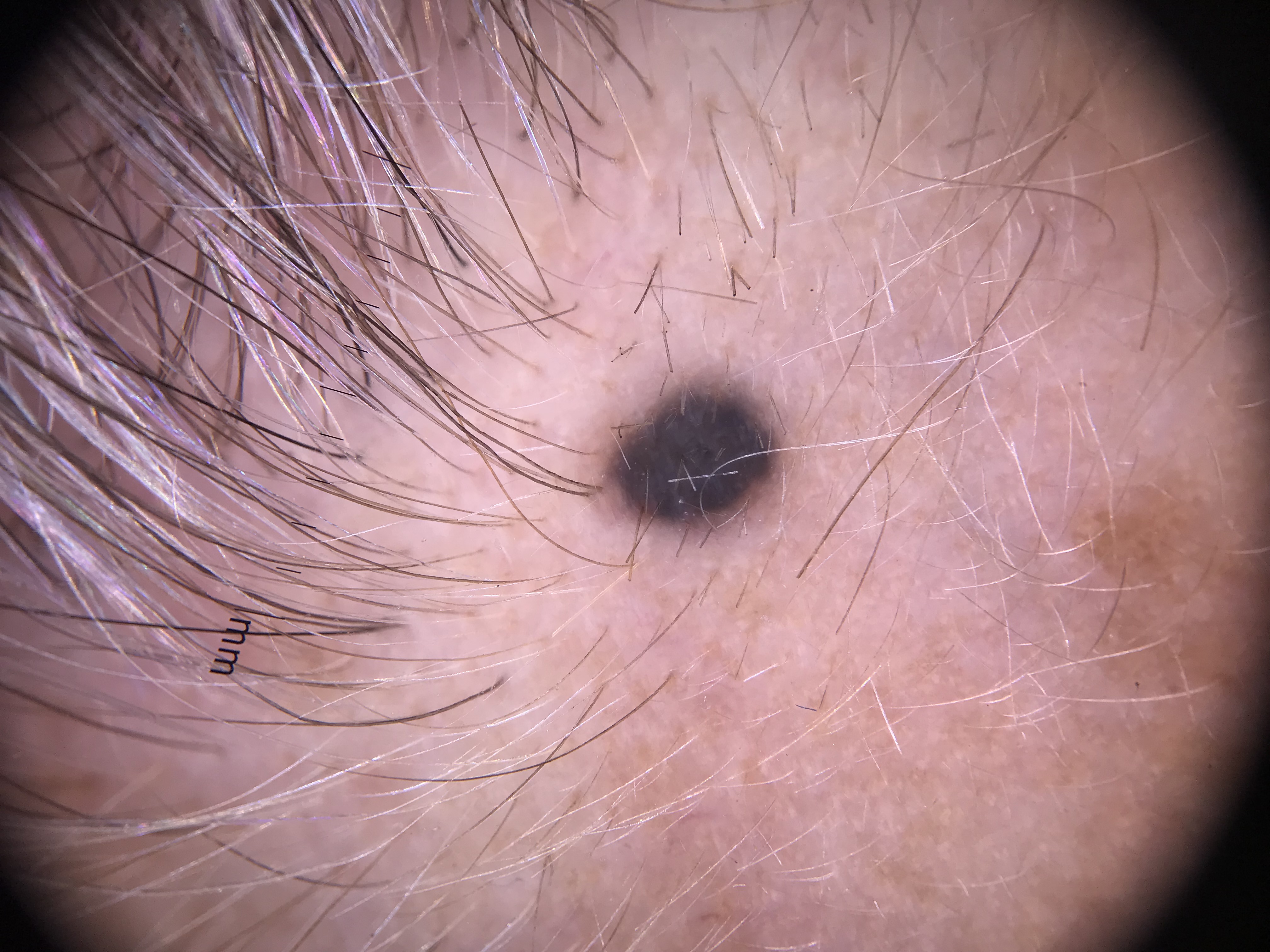A dermoscopic image of a skin lesion.
Consistent with a banal lesion — a blue nevus.